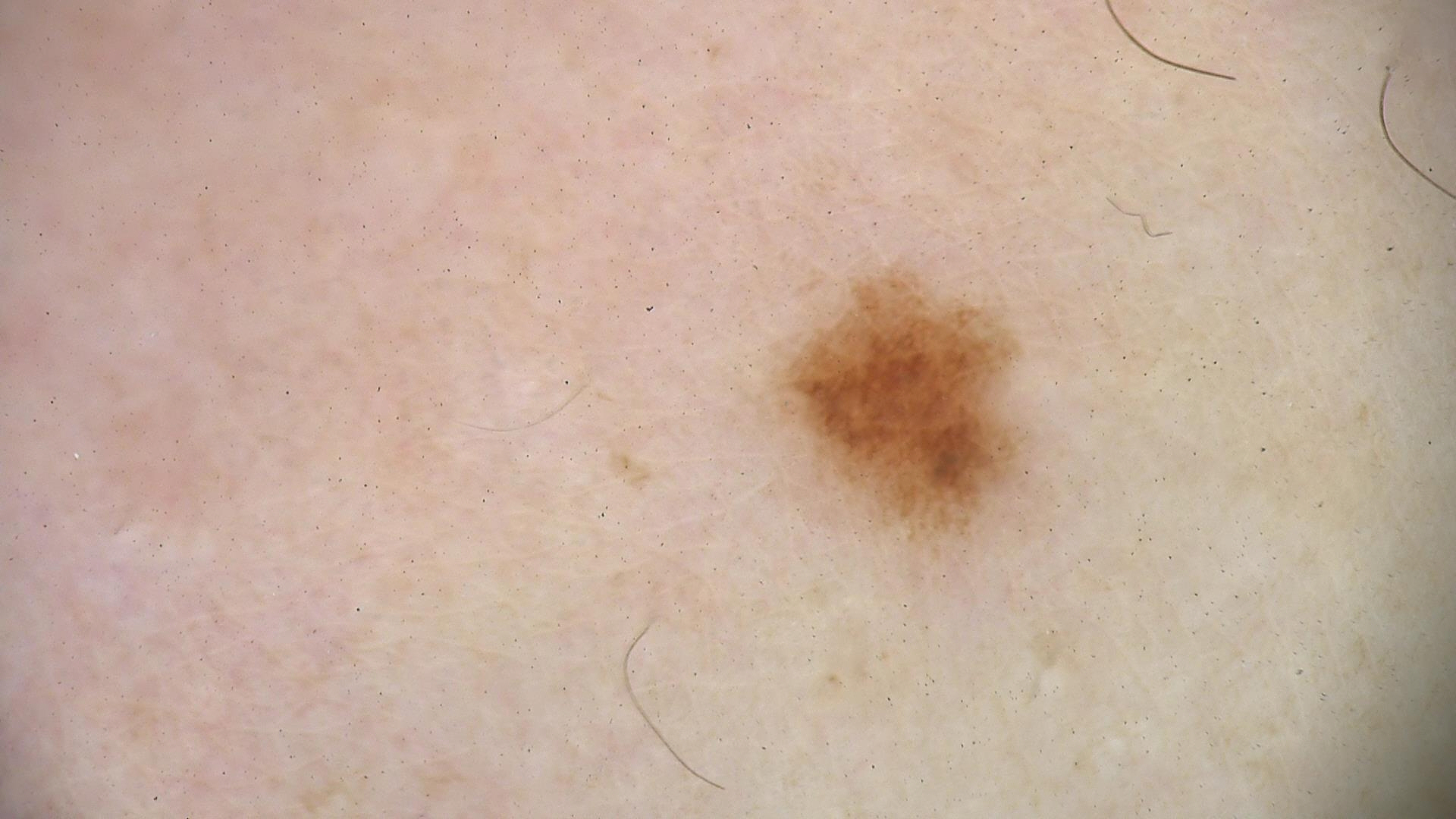* diagnosis · dysplastic junctional nevus (expert consensus)